The affected area is the top or side of the foot · texture is reported as raised or bumpy · present for more than five years · an image taken at a distance · symptoms reported: bothersome appearance · the patient considered this a nail problem.
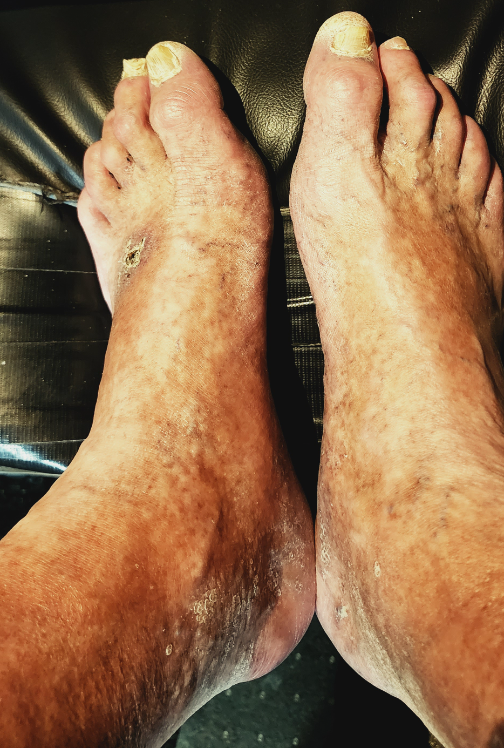Q: What conditions are considered?
A: Onychomycosis (most likely); Psoriasis (unlikely); Pachyonychia congenita (unlikely); Lichen planus/lichenoid eruption (unlikely)